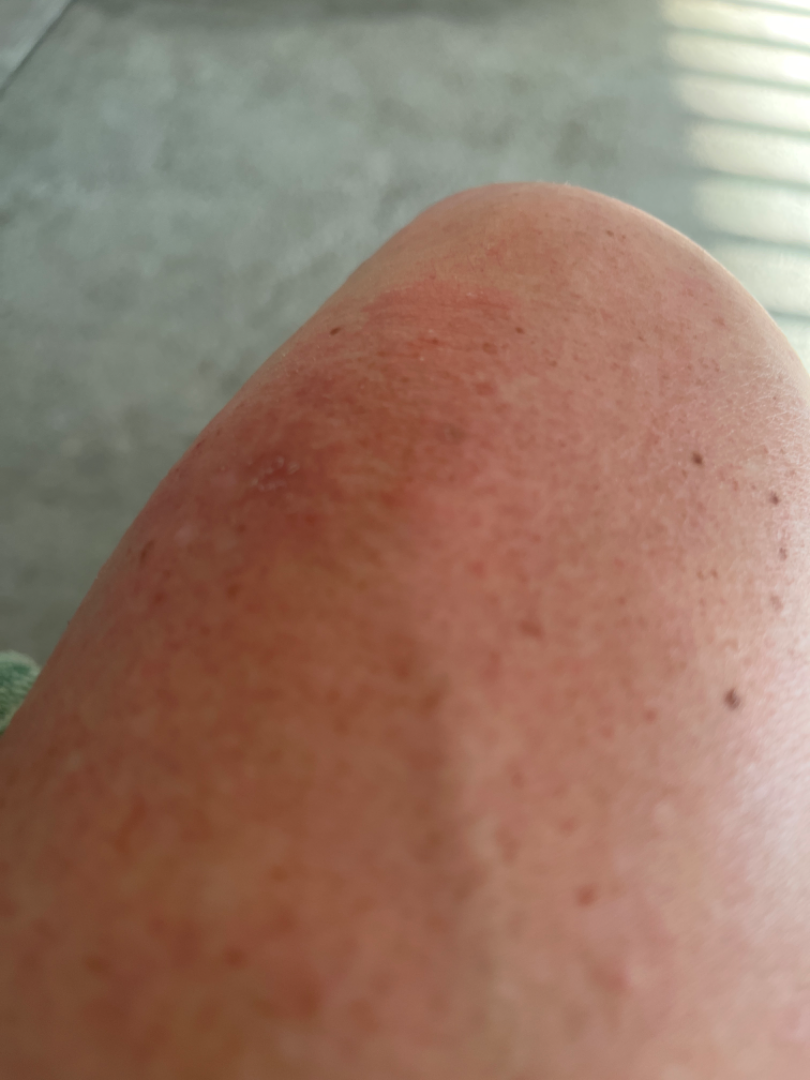| feature | finding |
|---|---|
| site | leg |
| surface texture | raised or bumpy |
| photo taken | at an angle |
| onset | one to three months |
| self-categorized as | a rash |
| contributor | female, age 50–59 |
| differential | the leading impression is Eczema; with consideration of Allergic Contact Dermatitis; also raised was Abrasion, scrape, or scab; less probable is Psoriasis |